The patient is a female roughly 55 years of age; a dermoscopic close-up of a skin lesion.
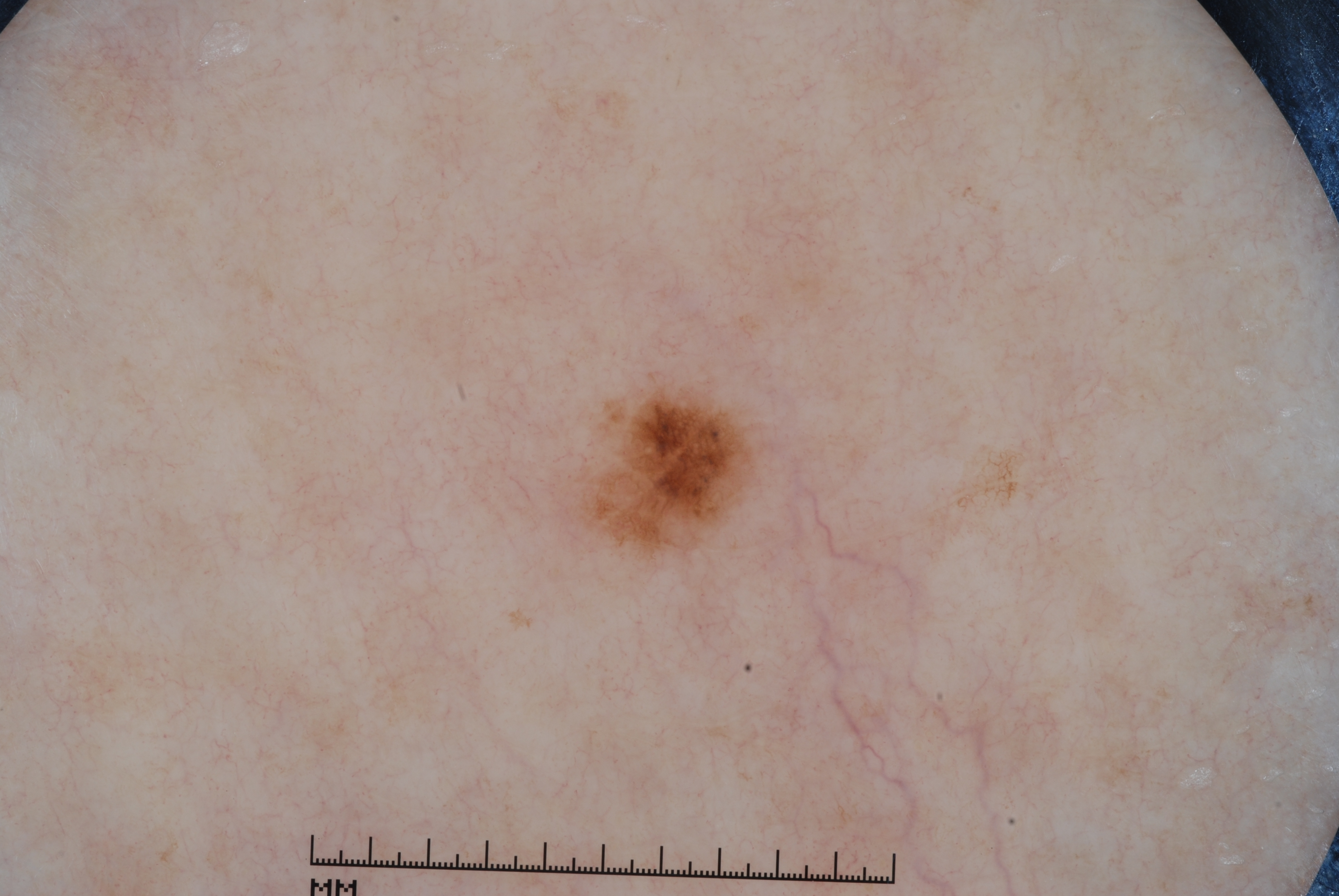On dermoscopy, the lesion shows pigment network. The lesion spans 565/393/753/553. Clinically diagnosed as a melanocytic nevus, a benign skin lesion.